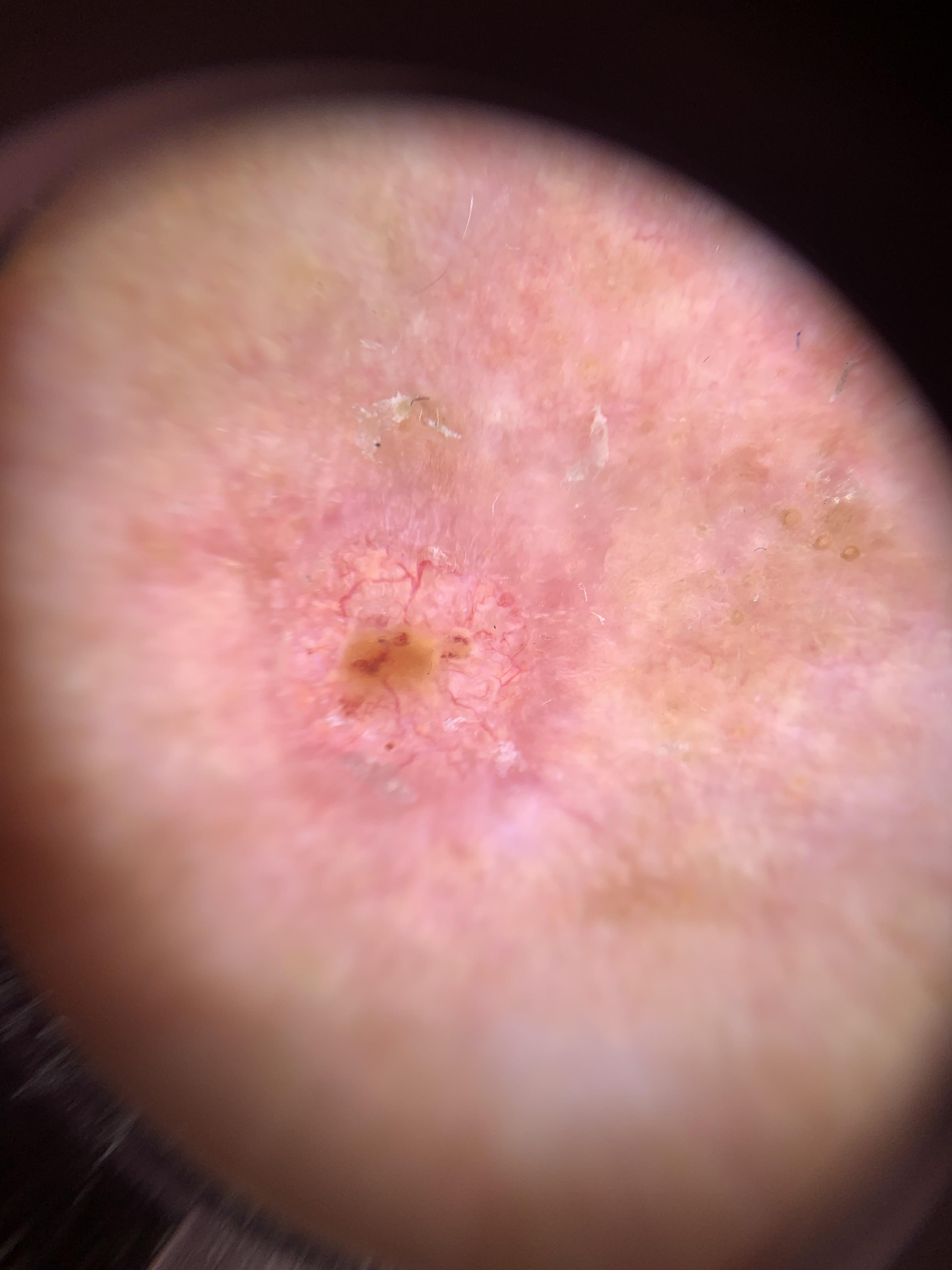Findings: Fitzpatrick skin type II. A male subject aged 83 or older. Conclusion: Confirmed on histopathology as a lesion of adnexal (follicular) origin — a basal cell carcinoma.